A dermoscopic photograph of a skin lesion:
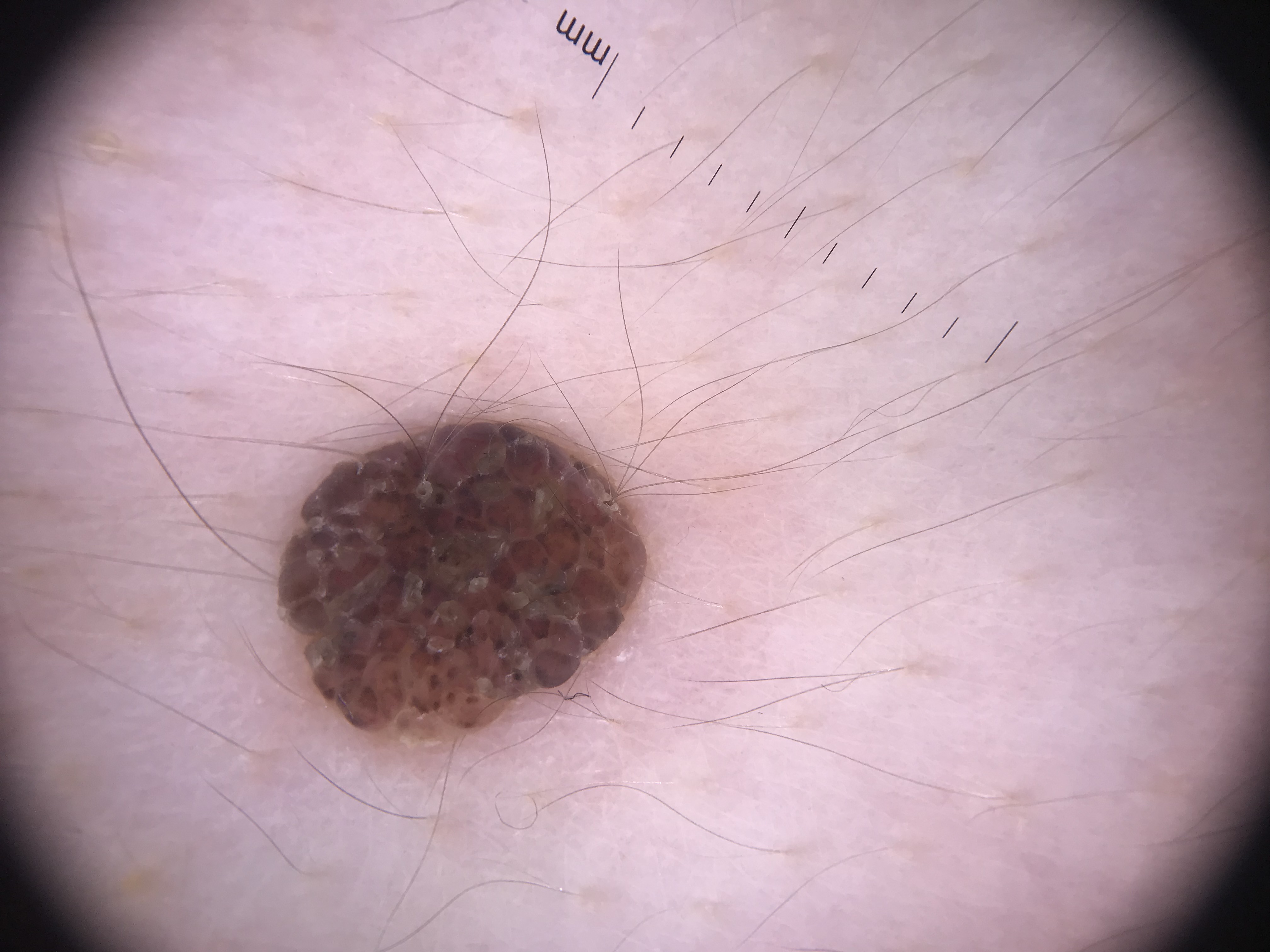Classified as a banal lesion — a compound nevus.